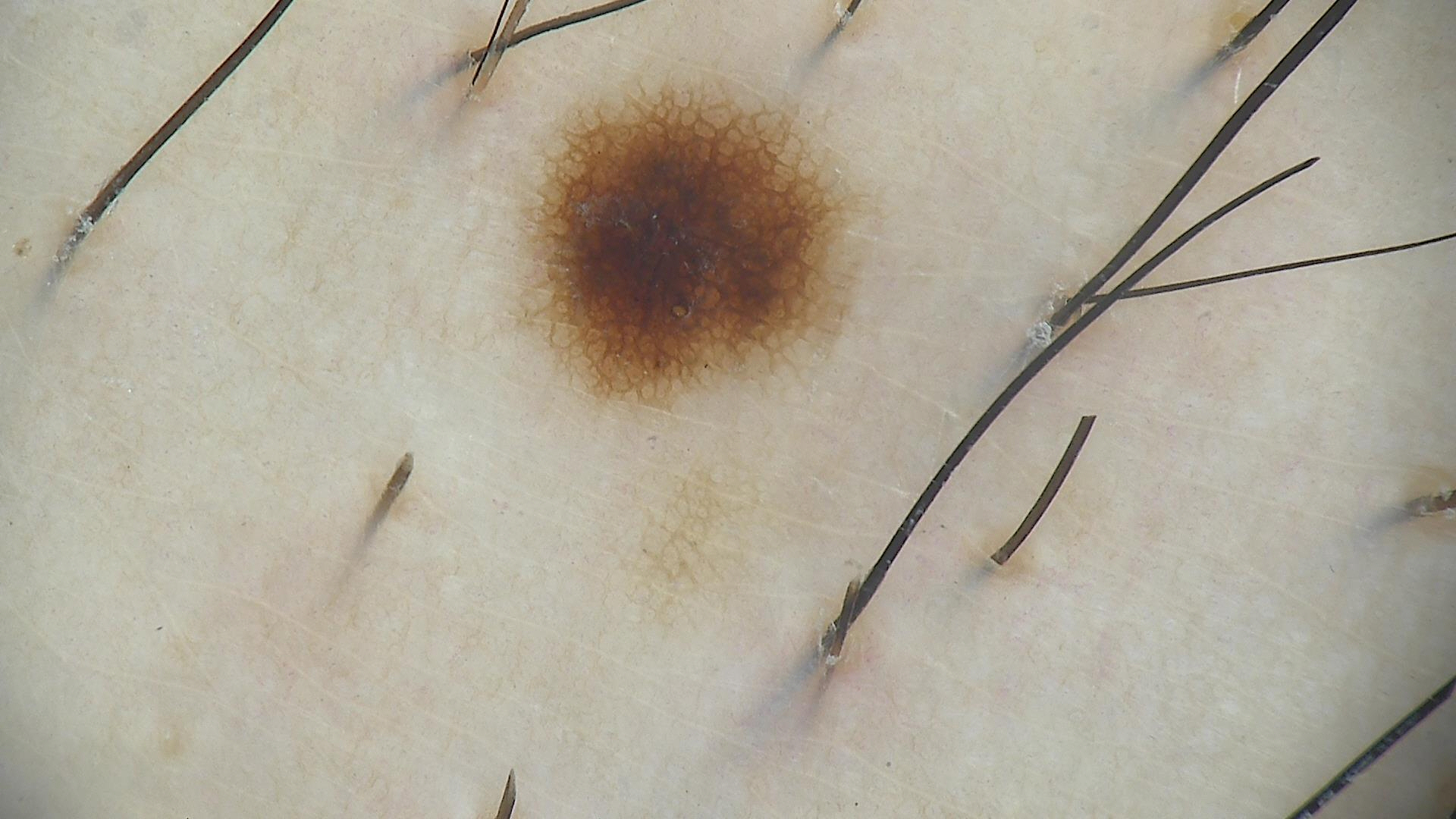Conclusion: The diagnostic label was a dysplastic junctional nevus.